A close-up photograph — 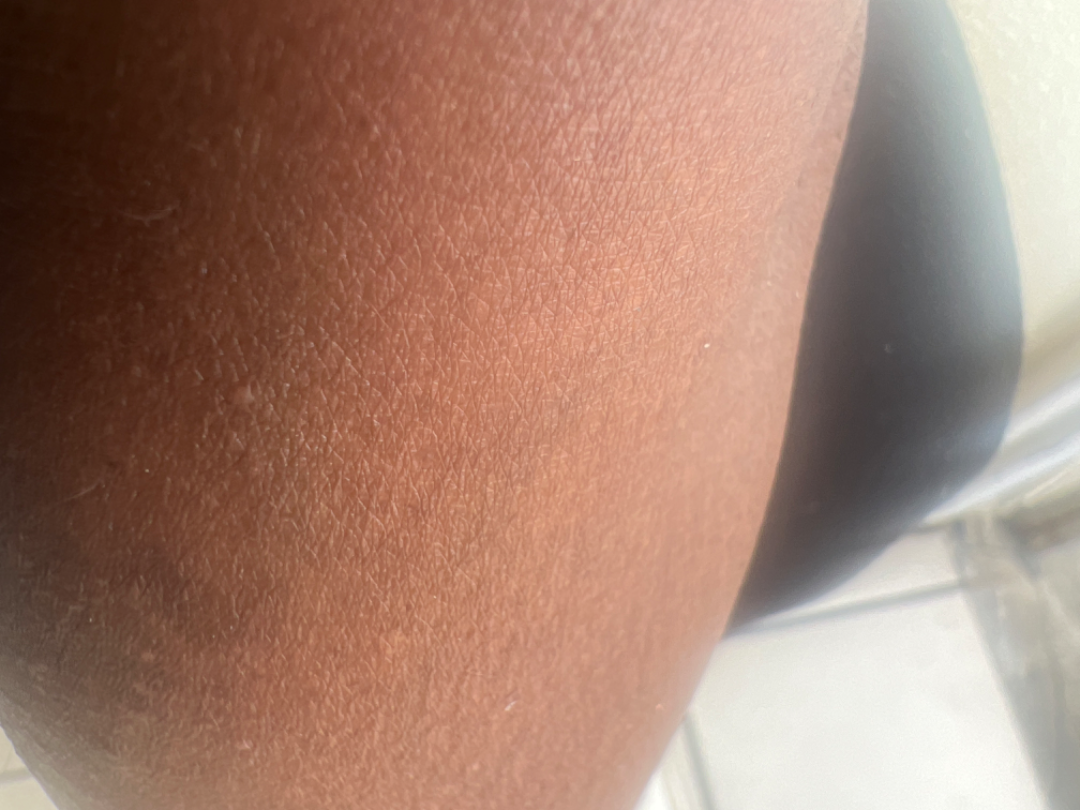assessment = could not be assessed